Dermoscopy of a skin lesion.
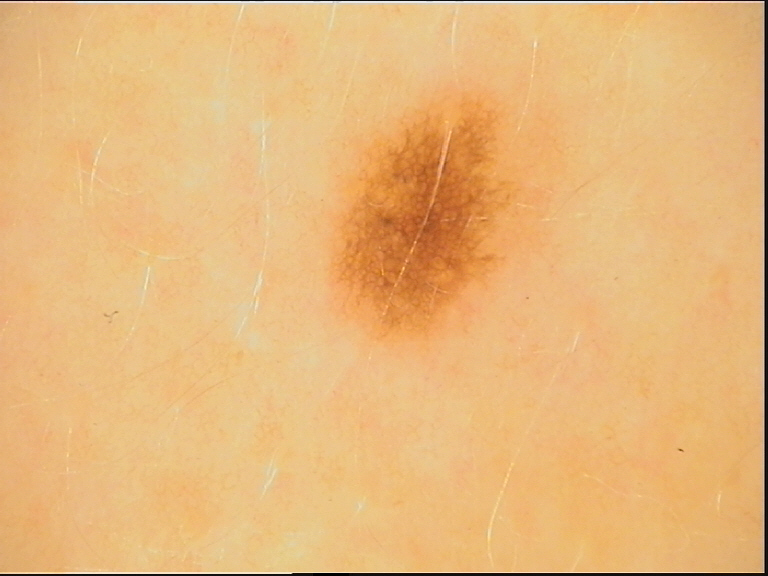diagnostic label=dysplastic junctional nevus (expert consensus).